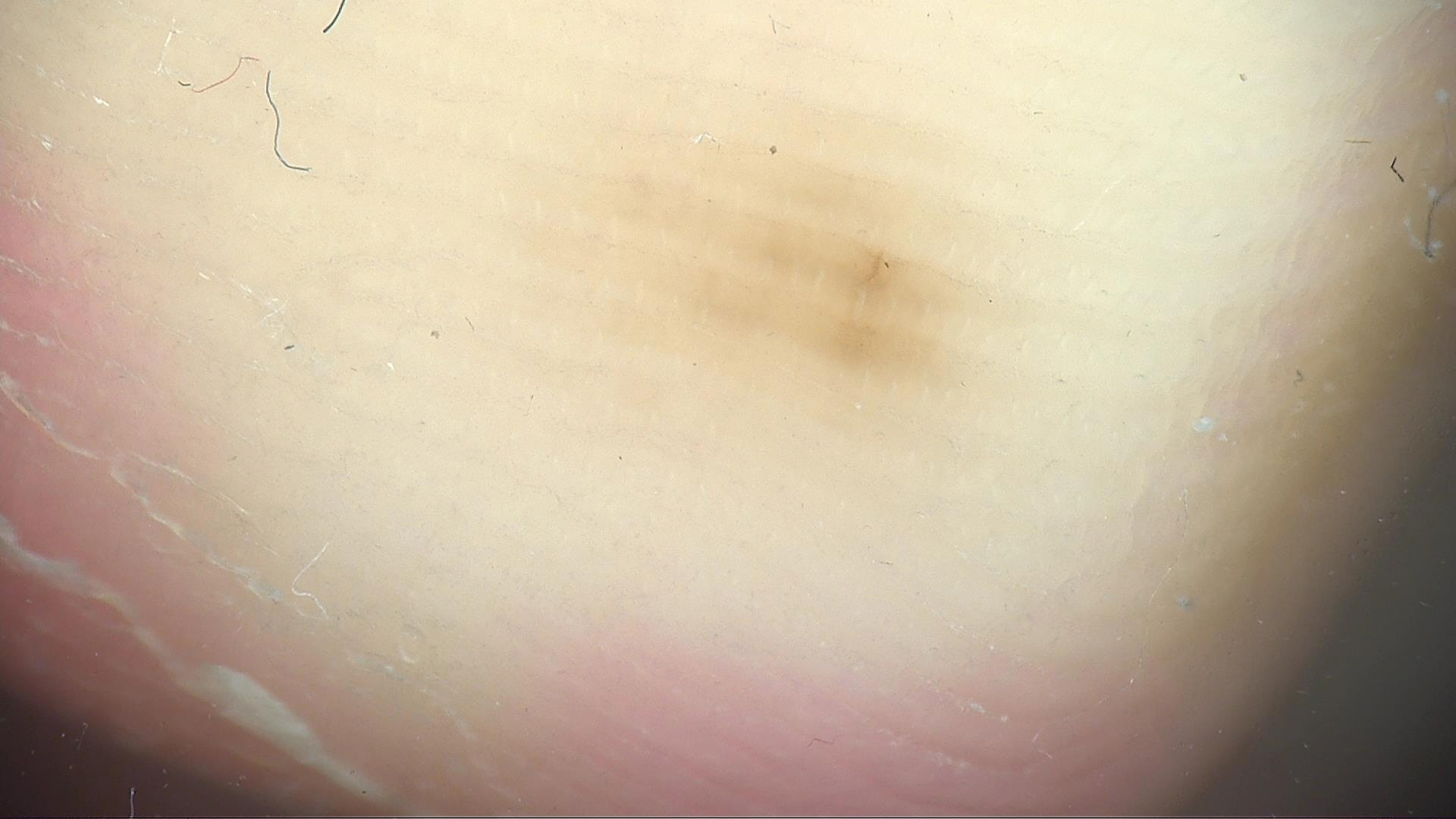{
  "lesion_type": {
    "main_class": "banal",
    "pattern": "junctional"
  },
  "diagnosis": {
    "name": "acral junctional nevus",
    "code": "ajb",
    "malignancy": "benign",
    "super_class": "melanocytic",
    "confirmation": "expert consensus"
  }
}